A male subject aged 78 to 82. A dermatoscopic image of a skin lesion — 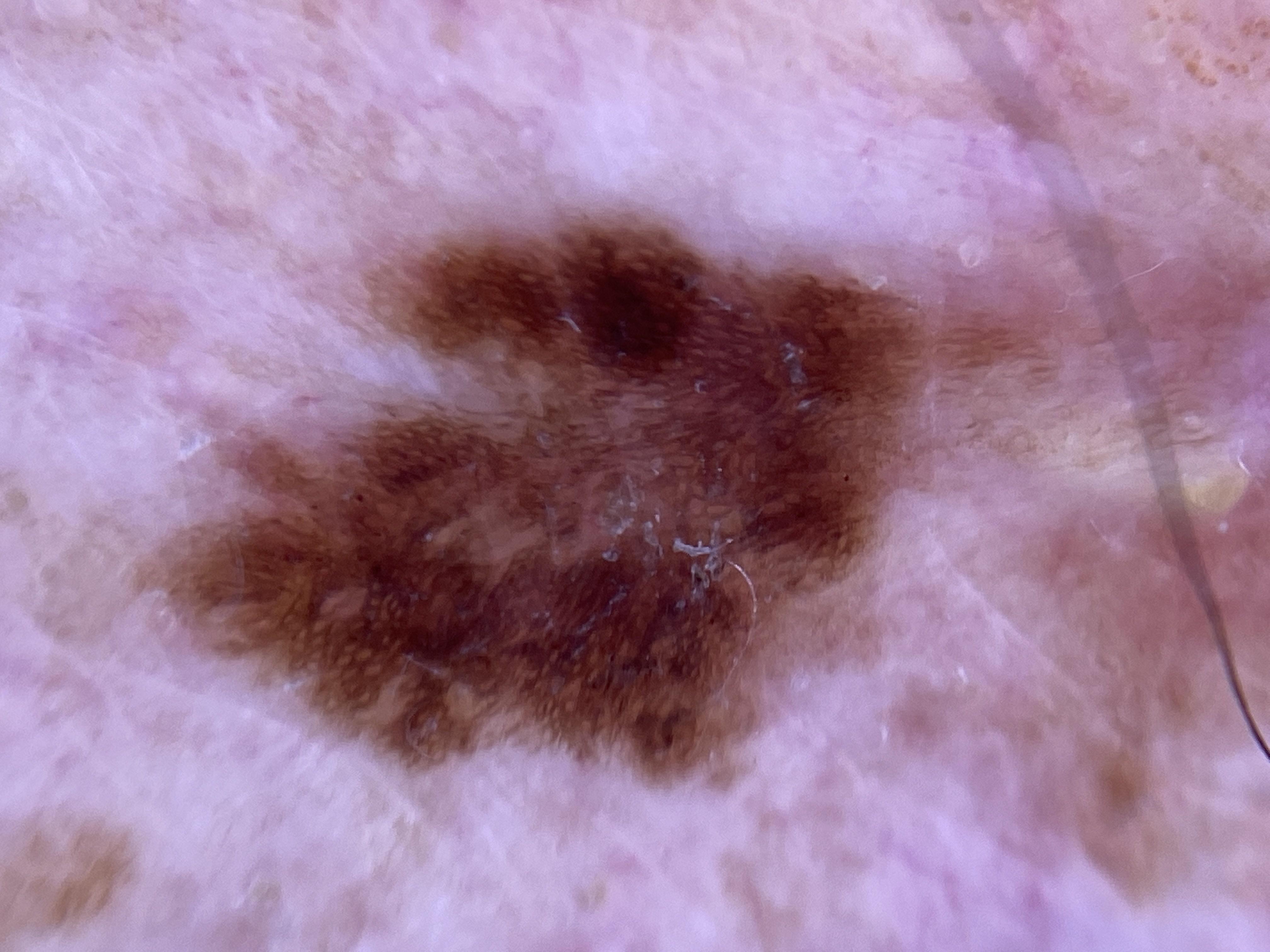Clinical context:
The lesion involves the posterior trunk.
Conclusion:
Confirmed on histopathology as a benign lesion — a nevus.